Referred with a clinical suspicion of basal cell carcinoma · a moderate number of moles by the patient's own estimate · the patient reports a family history of skin cancer and a personal history of cancer · a female subject 64 years old · the patient says their skin tans without first burning · a skin lesion imaged with a dermatoscope.
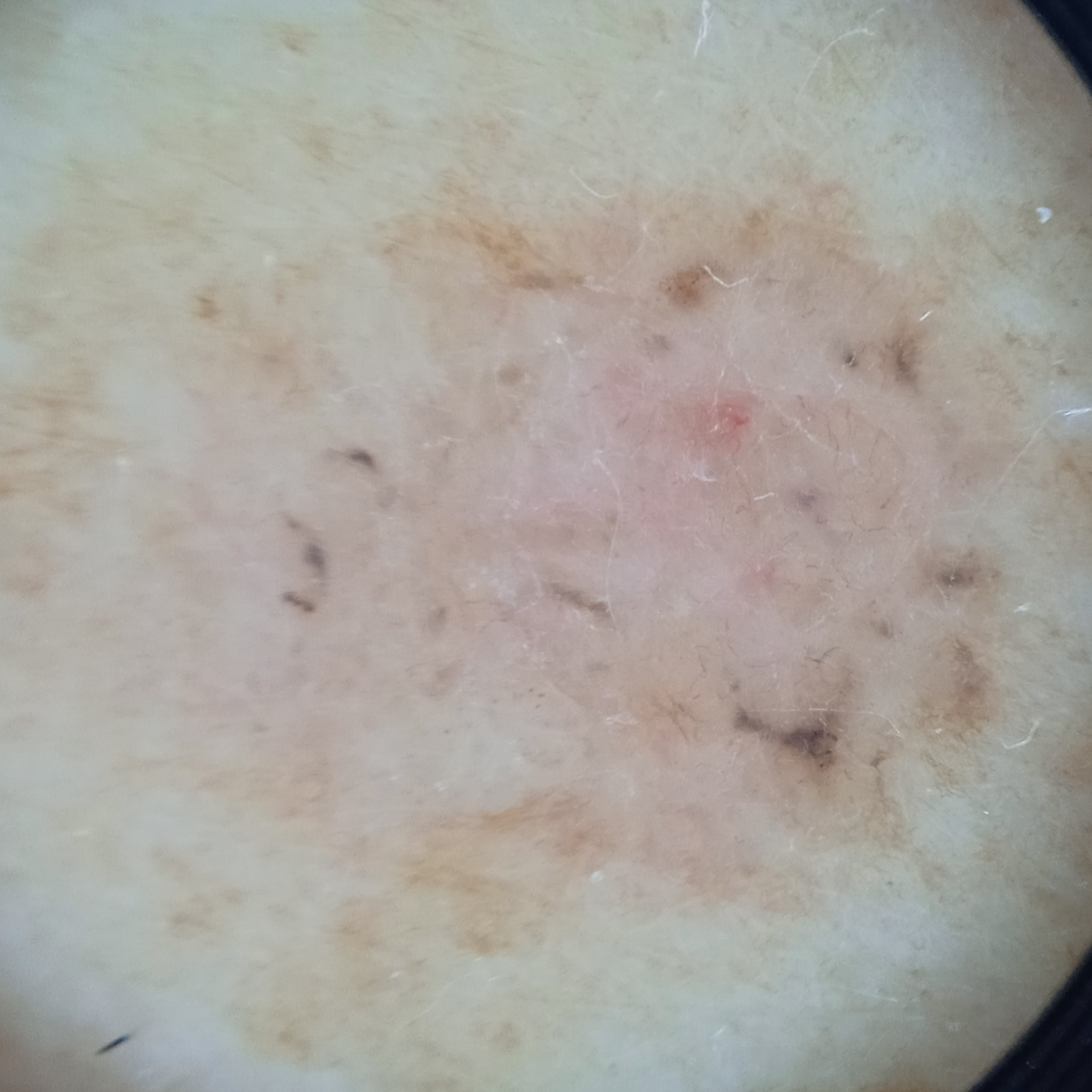location: the back; diameter: 9.8 mm; pathology: basal cell carcinoma (biopsy-proven).